Dermoscopy of a skin lesion.
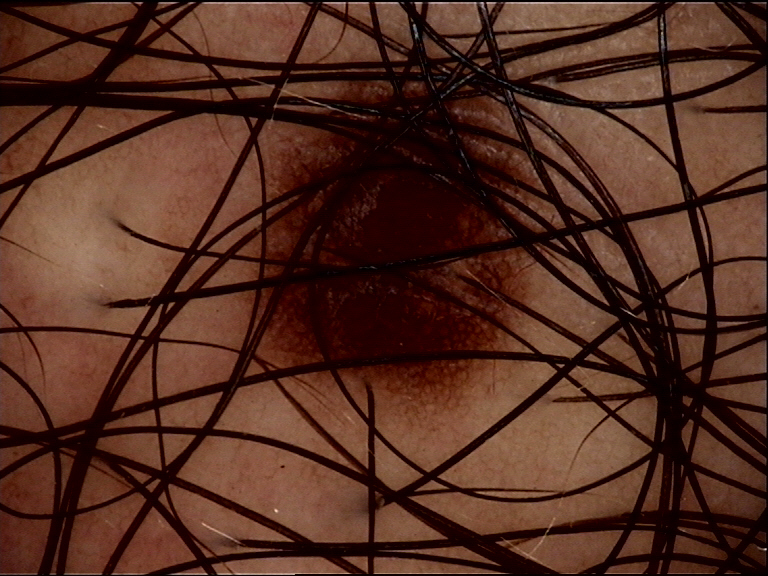{
  "lesion_type": {
    "main_class": "banal",
    "pattern": "junctional"
  },
  "diagnosis": {
    "name": "junctional nevus",
    "code": "jb",
    "malignancy": "benign",
    "super_class": "melanocytic",
    "confirmation": "expert consensus"
  }
}